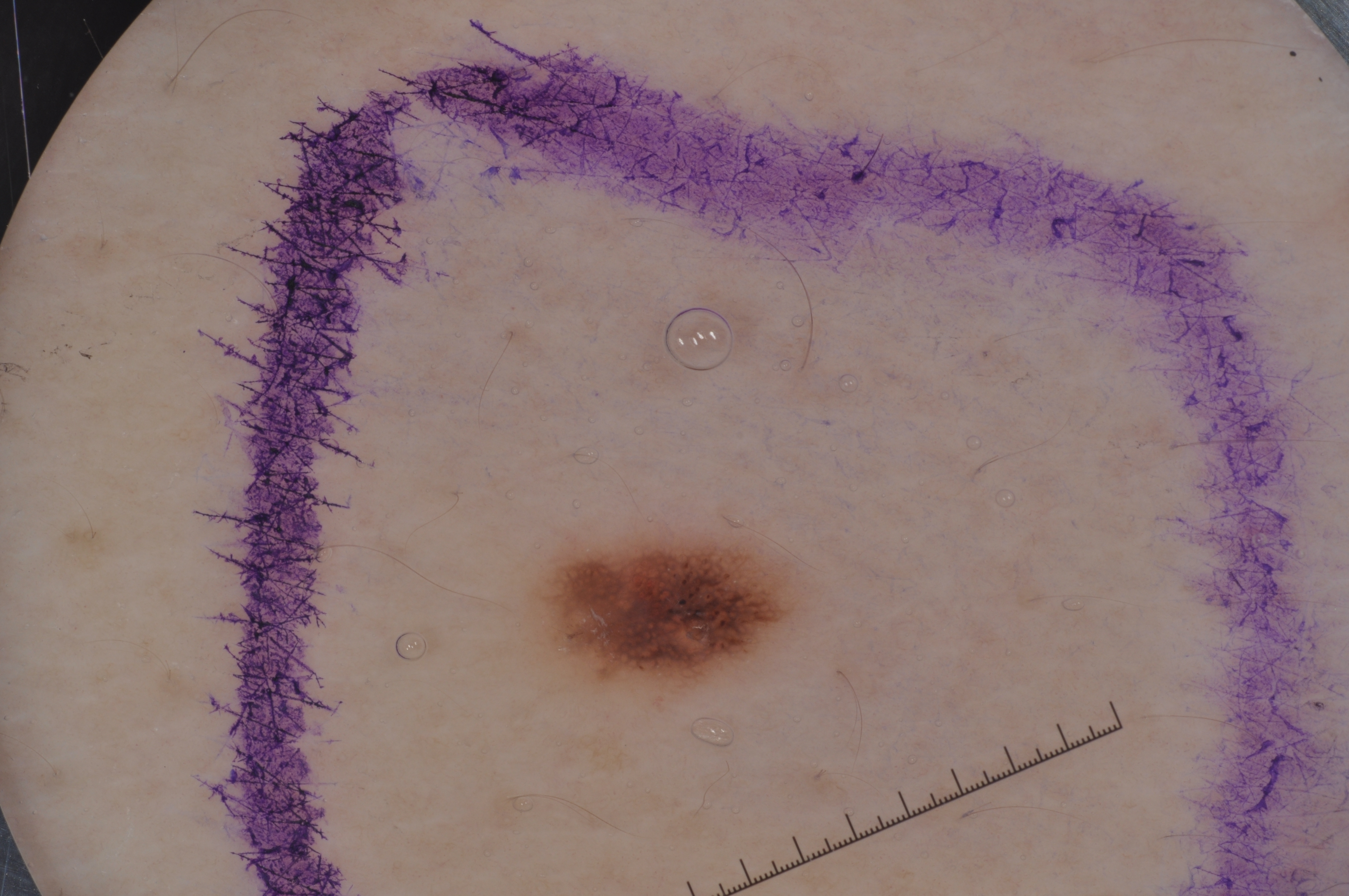Case summary: A dermoscopic close-up of a skin lesion. A male patient aged 28-32. The lesion covers approximately 3% of the dermoscopic field. Dermoscopic examination shows pigment network, with no milia-like cysts, negative network, or streaks. The lesion is located at x1=538 y1=533 x2=790 y2=693. Conclusion: Expert review diagnosed this as a melanocytic nevus.